A male subject age 58; the patient was assessed as FST II — 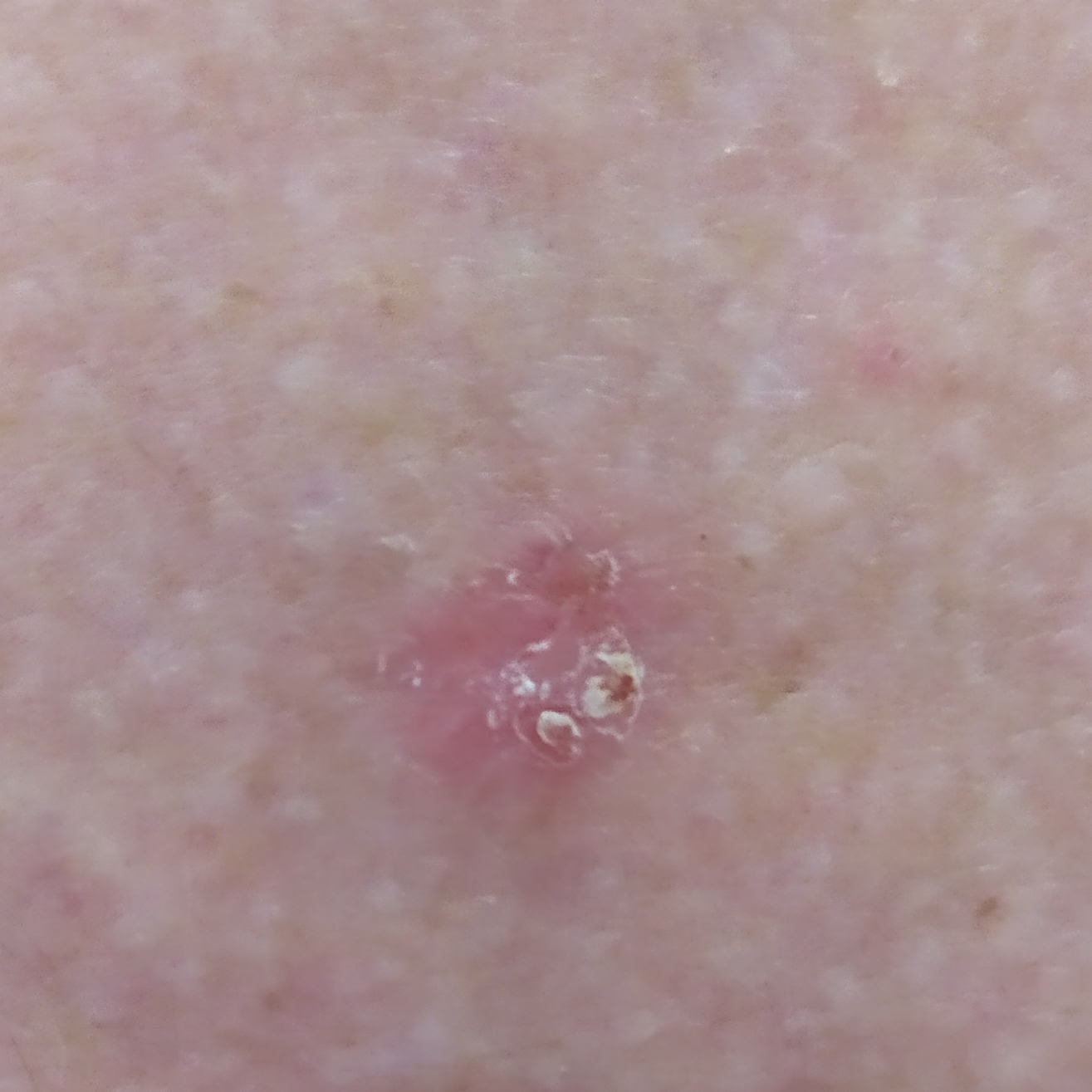<skin_lesion>
  <lesion_location>the back</lesion_location>
  <lesion_size>
    <diameter_1_mm>10.0</diameter_1_mm>
    <diameter_2_mm>7.0</diameter_2_mm>
  </lesion_size>
  <symptoms>
    <absent>bleeding</absent>
  </symptoms>
  <diagnosis>
    <name>squamous cell carcinoma</name>
    <code>SCC</code>
    <malignancy>malignant</malignancy>
    <confirmation>histopathology</confirmation>
  </diagnosis>
</skin_lesion>